A dermatoscopic image of a skin lesion: 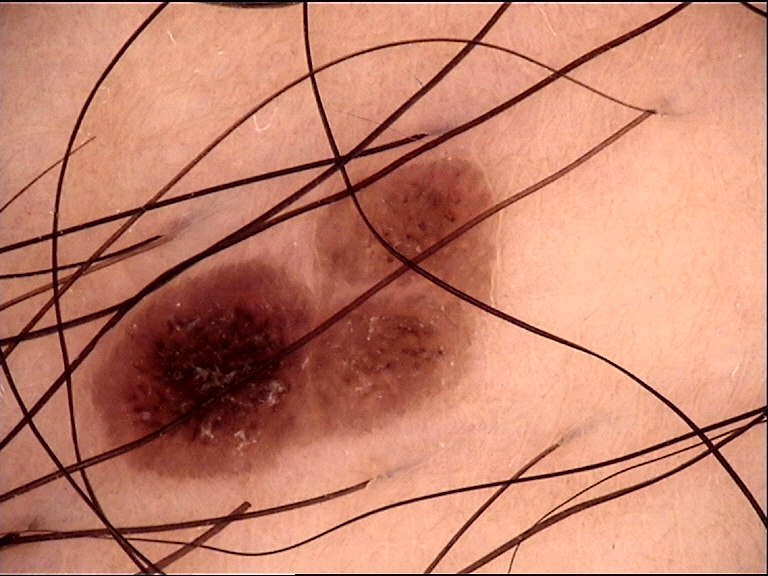Diagnosed as a dysplastic compound nevus.